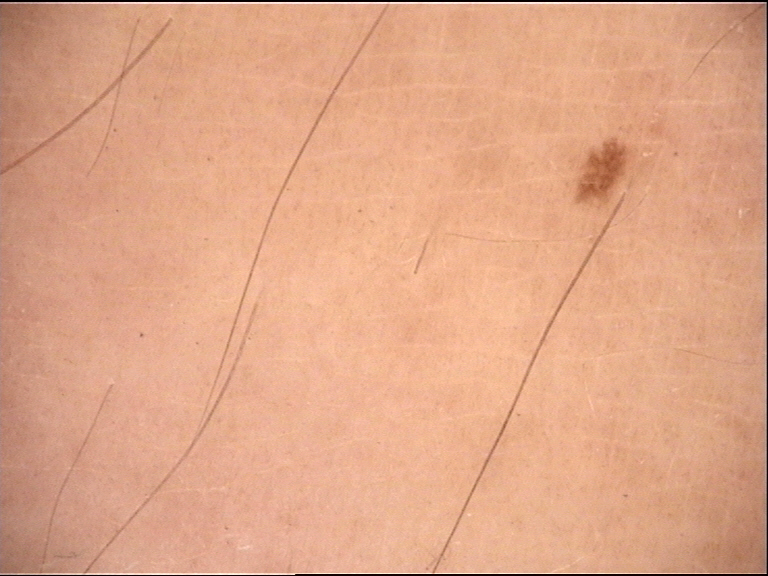<dermoscopy>
  <diagnosis>
    <name>junctional nevus</name>
    <code>jb</code>
    <malignancy>benign</malignancy>
    <super_class>melanocytic</super_class>
    <confirmation>expert consensus</confirmation>
  </diagnosis>
</dermoscopy>